A skin lesion imaged with a dermatoscope.
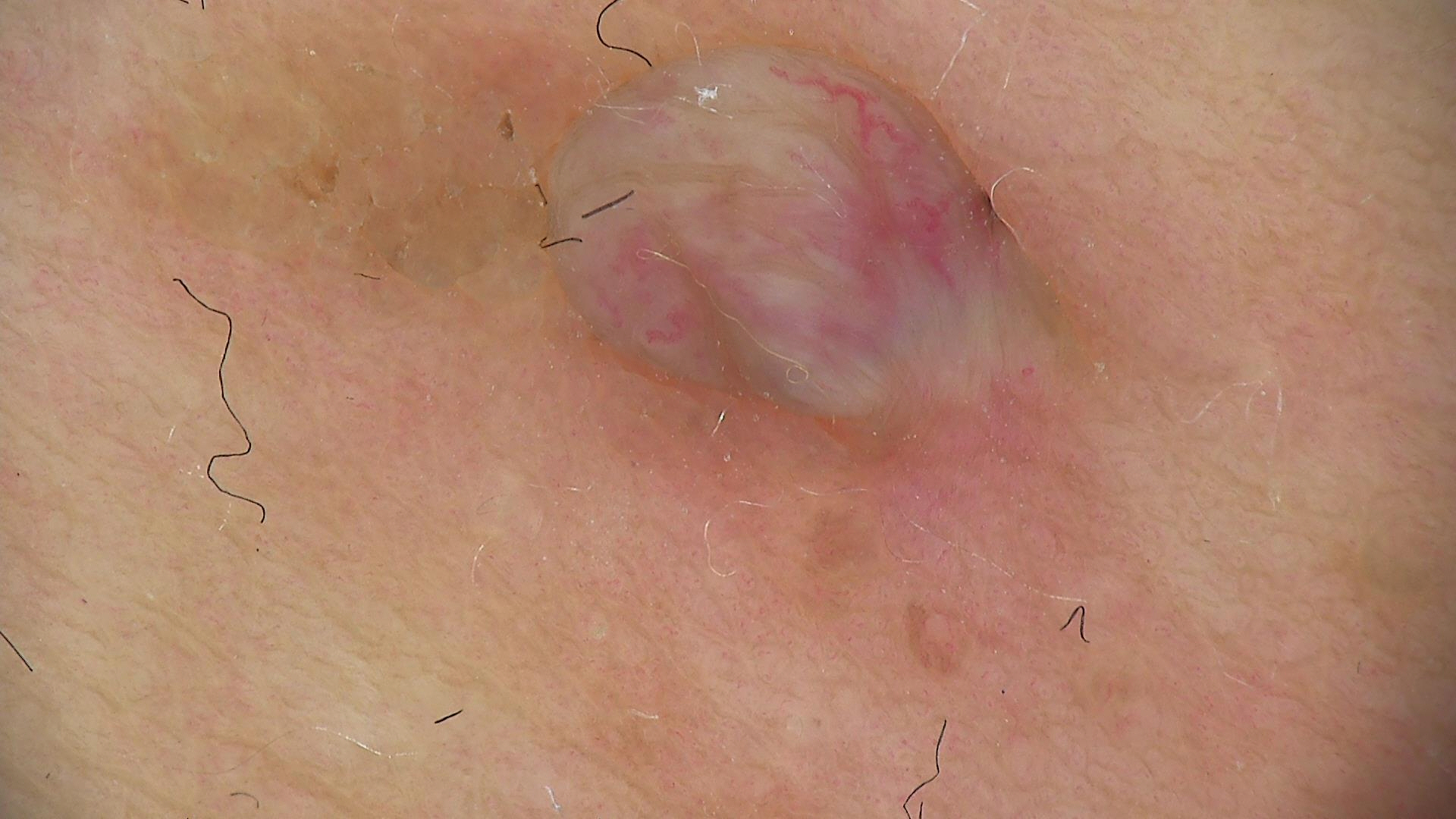Findings:
- subtype · banal
- diagnostic label · dermal nevus (expert consensus)